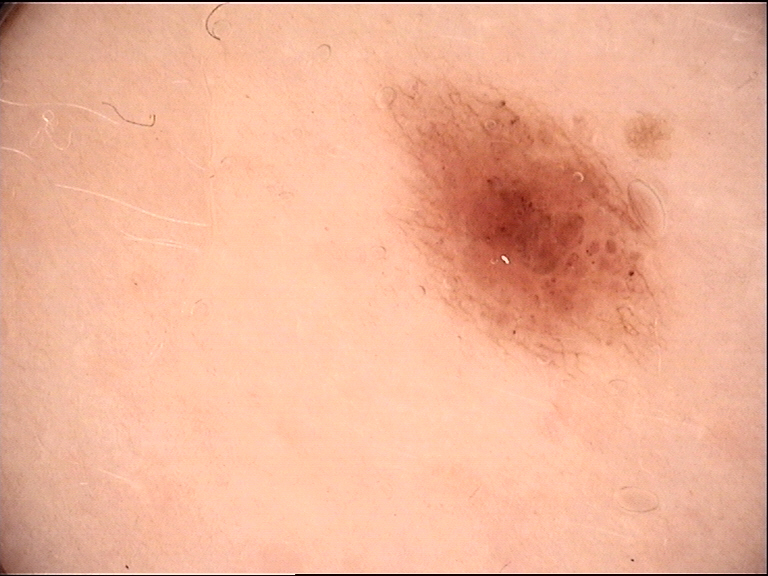| field | value |
|---|---|
| modality | dermoscopy |
| label | dysplastic compound nevus (expert consensus) |